A dermoscopic image of a skin lesion:
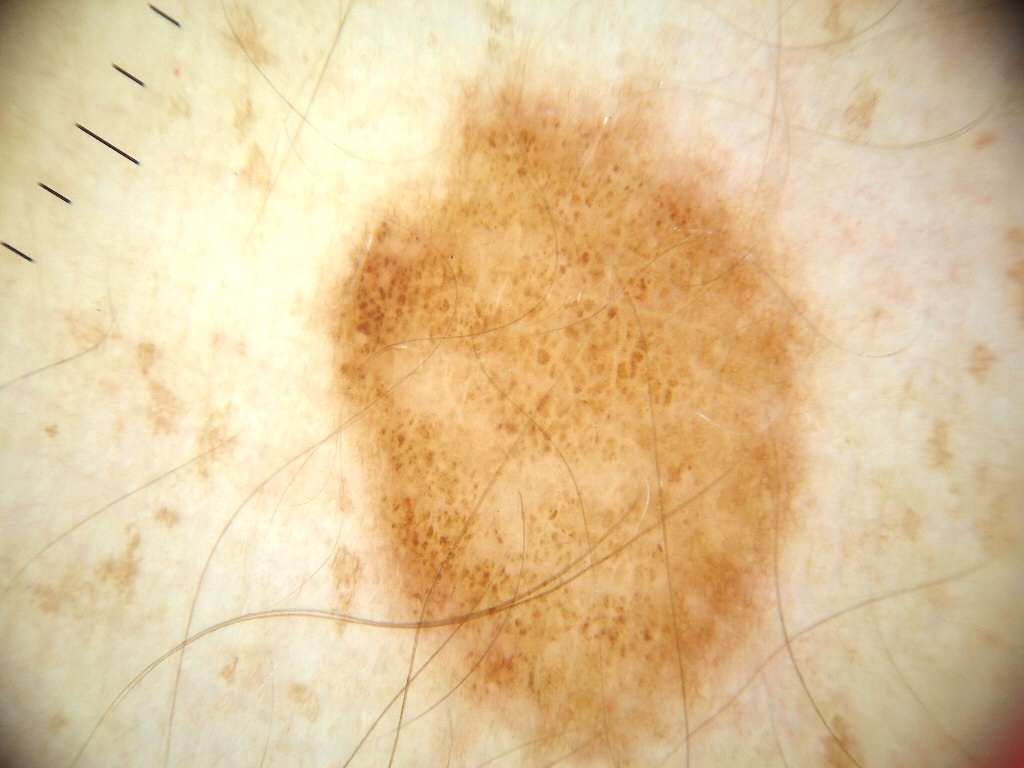bounding box: [306, 43, 839, 762]
assessment: a melanocytic nevus